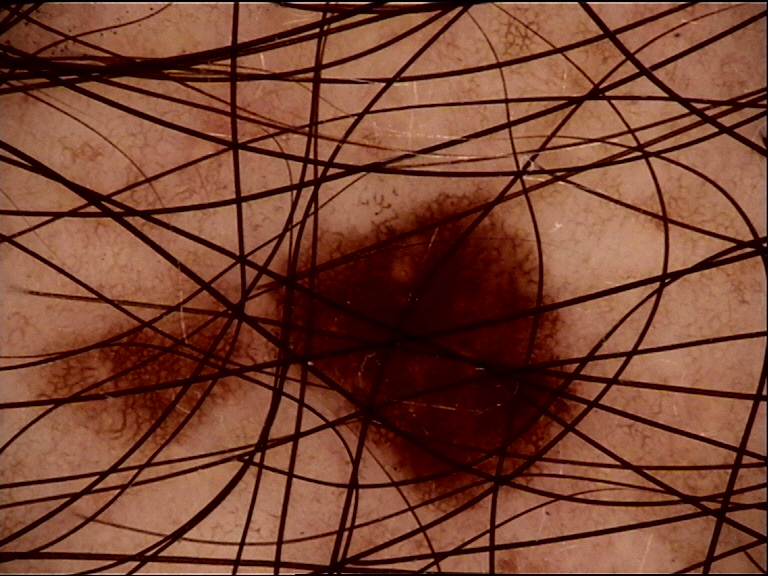Findings:
* label · dysplastic junctional nevus (expert consensus)